The patient says their skin reddens with sun exposure · by self-report, a personal history of skin cancer and a personal history of cancer · collected as part of a research study, without a referral diagnosis.
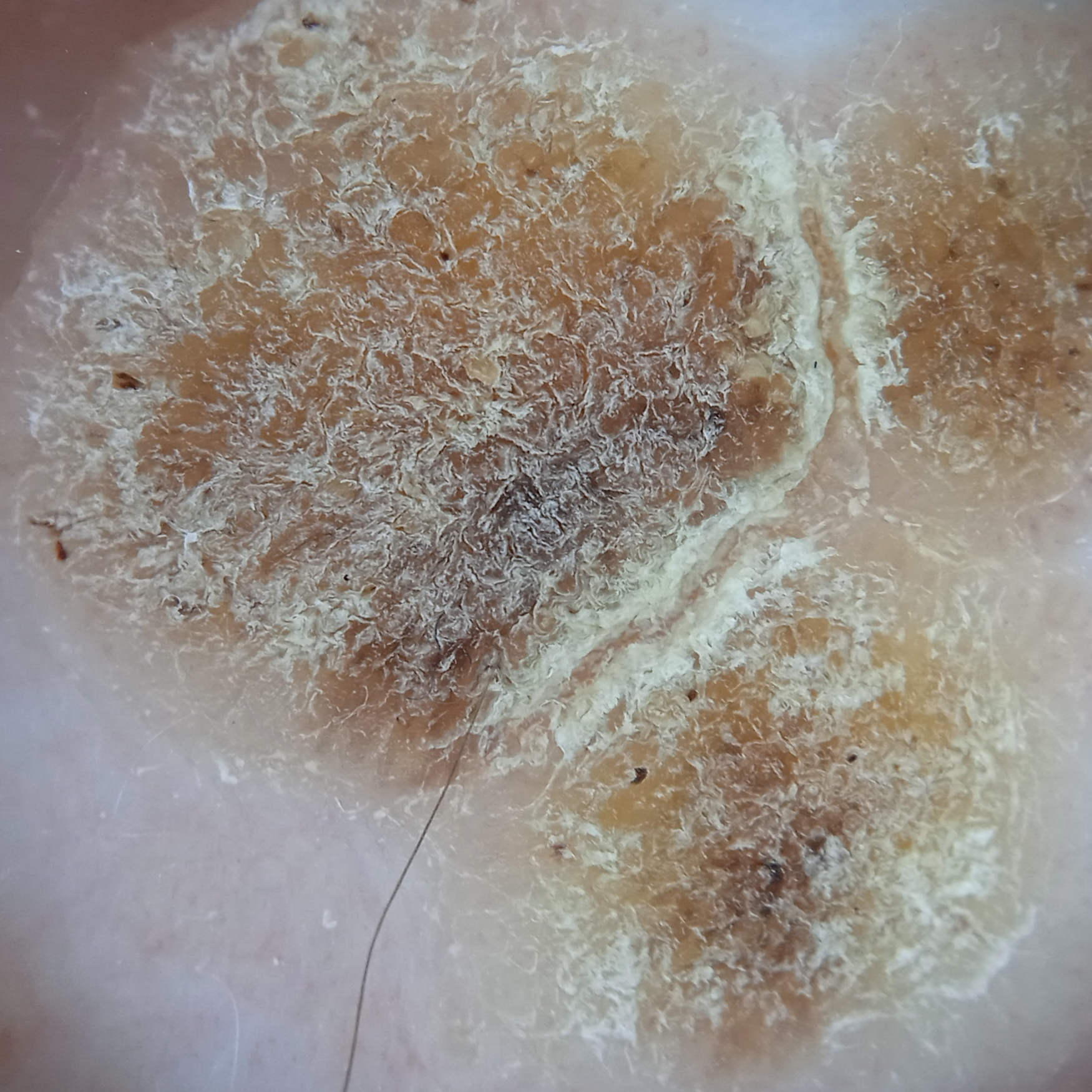anatomic site: the back
lesion size: 14.2 mm
diagnosis: seborrheic keratosis (dermatologist consensus)